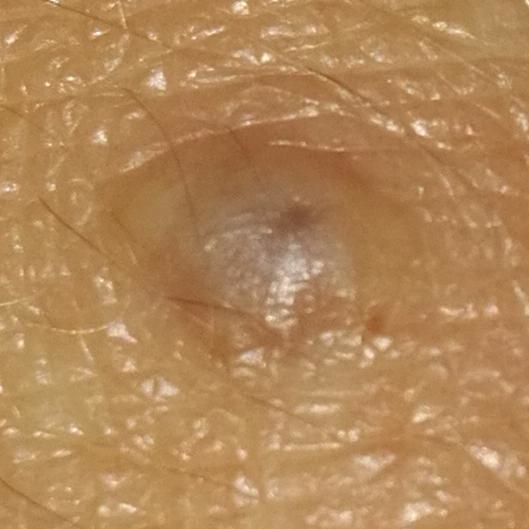Findings: A clinical close-up photograph of a skin lesion. A subject in their 30s. The lesion was found on a hand. By the patient's account, the lesion hurts, but does not itch. Conclusion: Consistent with a nevus.